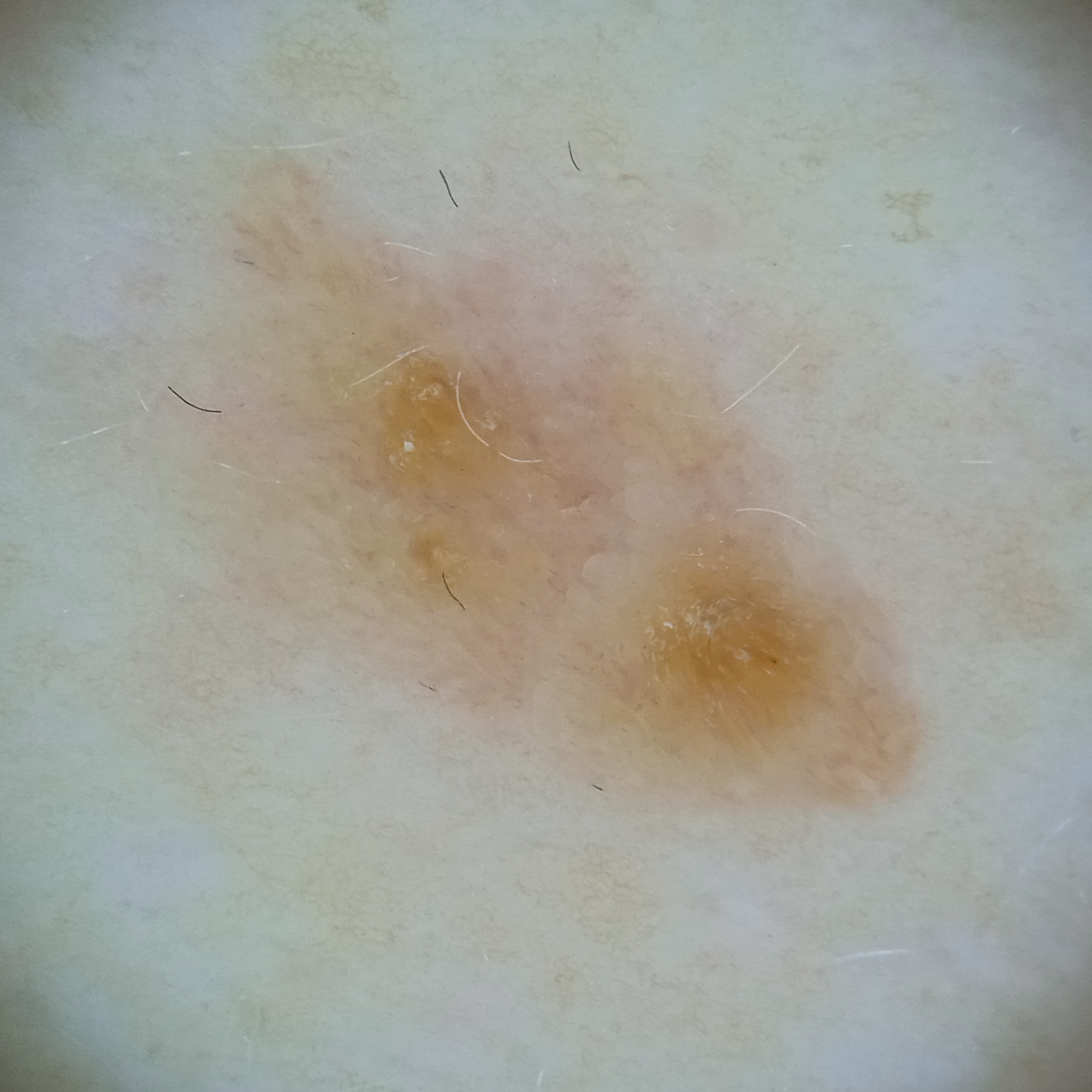Q: What is the imaging modality?
A: dermatoscopic image
Q: How does the patient's skin react to sun?
A: skin reddens with sun exposure
Q: Patient demographics?
A: female, age 59
Q: What is the patient's nevus burden?
A: a moderate number of melanocytic nevi
Q: Where is the lesion?
A: the torso
Q: How large is the lesion?
A: 9.1 mm
Q: What was the diagnosis?
A: seborrheic keratosis (dermatologist consensus)